The head or neck is involved; the contributor is a female aged 30–39; the contributor reports the lesion is flat, raised or bumpy and rough or flaky; close-up view — 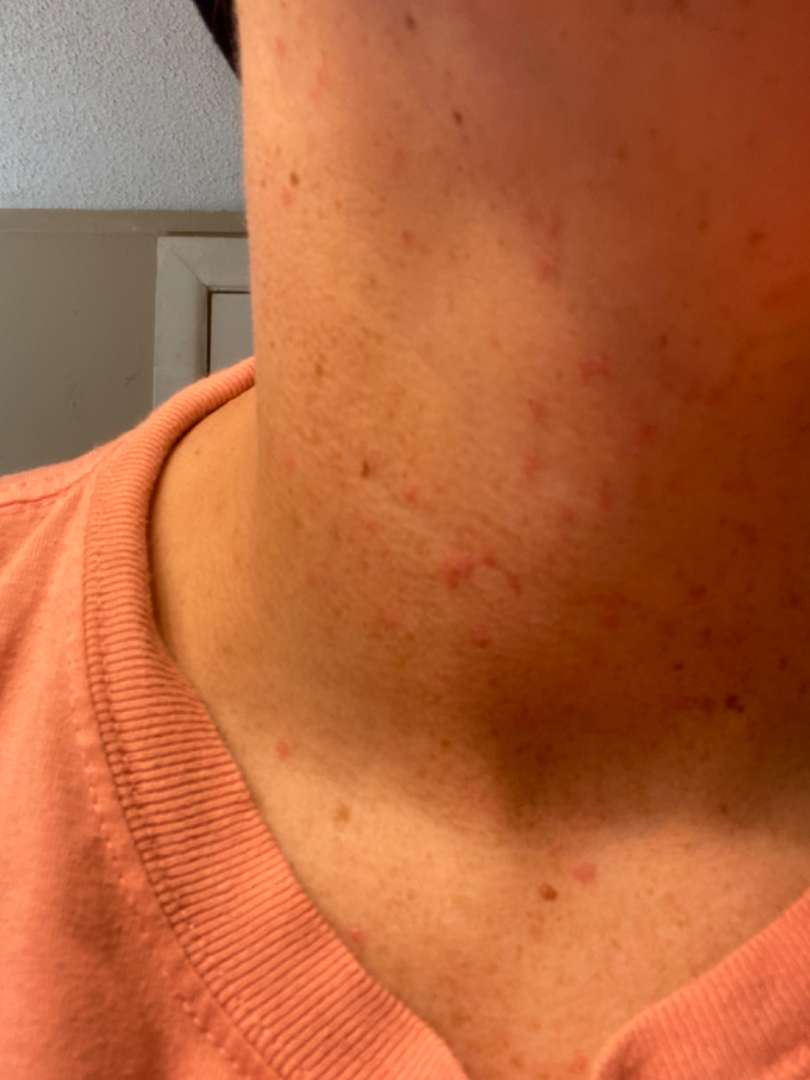| feature | finding |
|---|---|
| impression | Acne (leading); Folliculitis (considered); Allergic Contact Dermatitis (less likely) |